A dermoscopic photograph of a skin lesion: 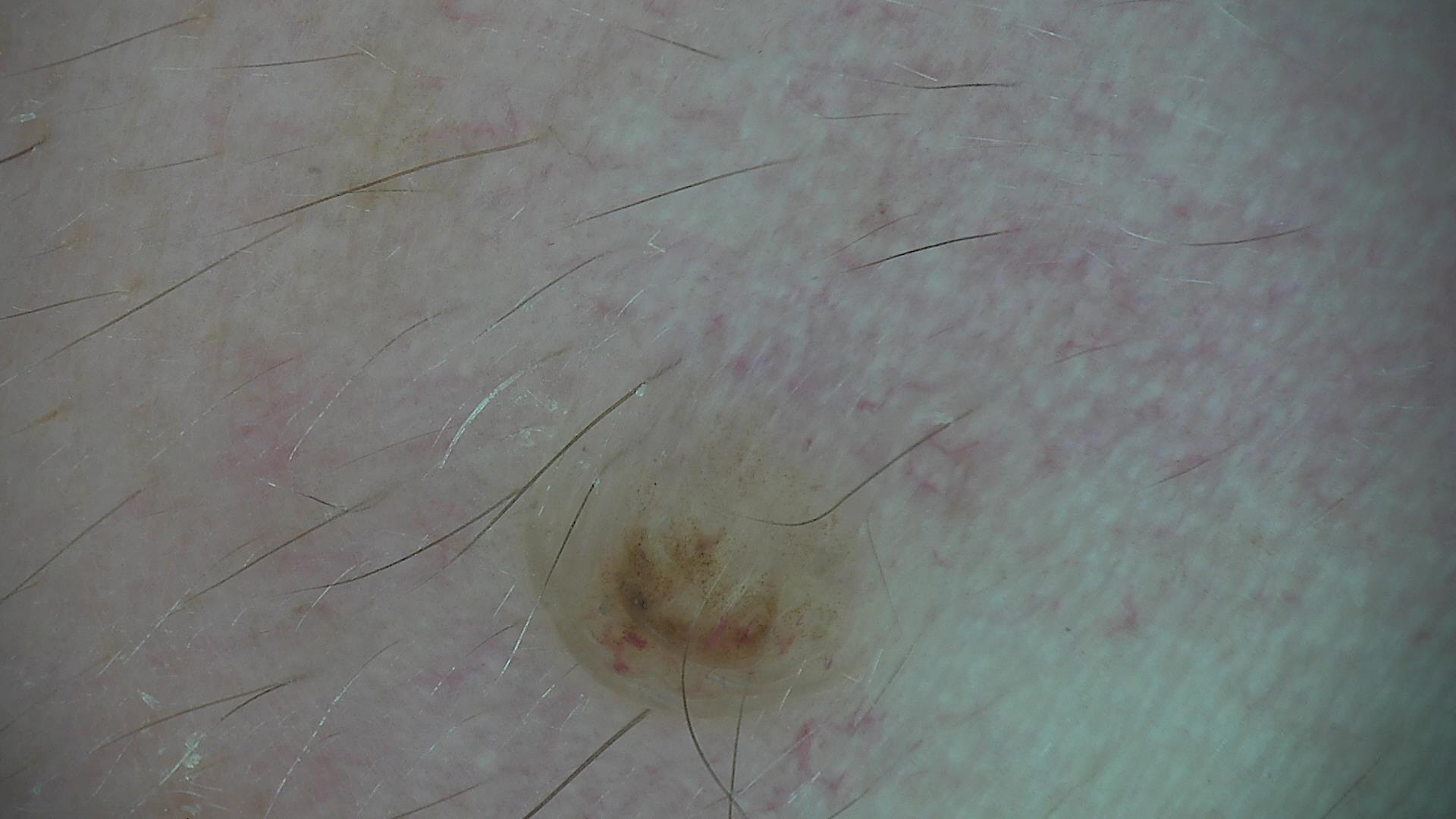The morphology is that of a banal lesion. Diagnosed as a dermal nevus.